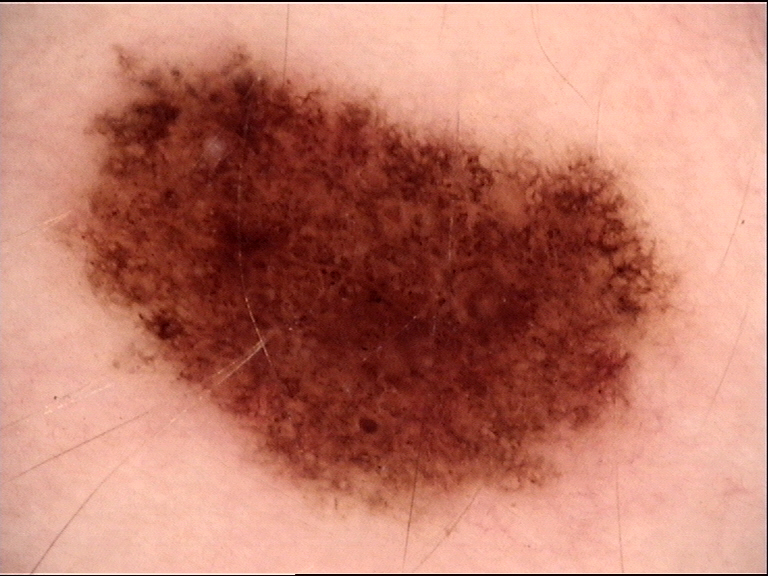image type: dermoscopy; class: dysplastic compound nevus (expert consensus).